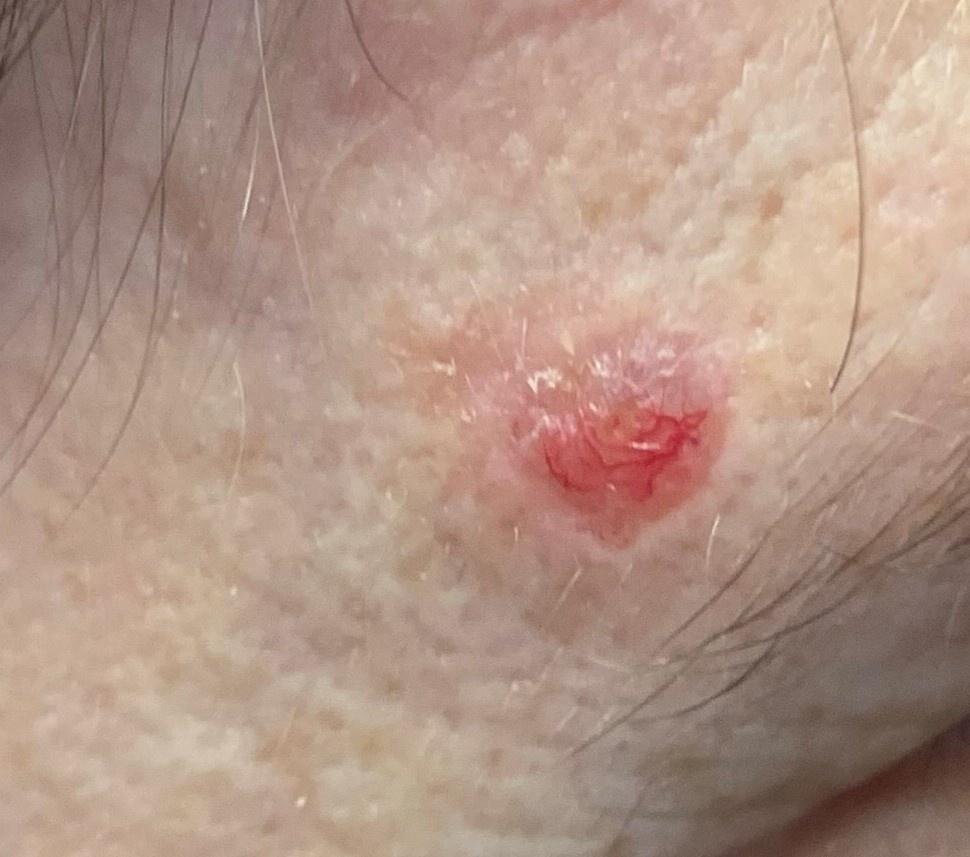The patient is FST II. An overview clinical photograph of a skin lesion. A female patient approximately 55 years of age. The lesion is located on the head or neck. Histopathological examination showed a malignancy — a basal cell carcinoma.